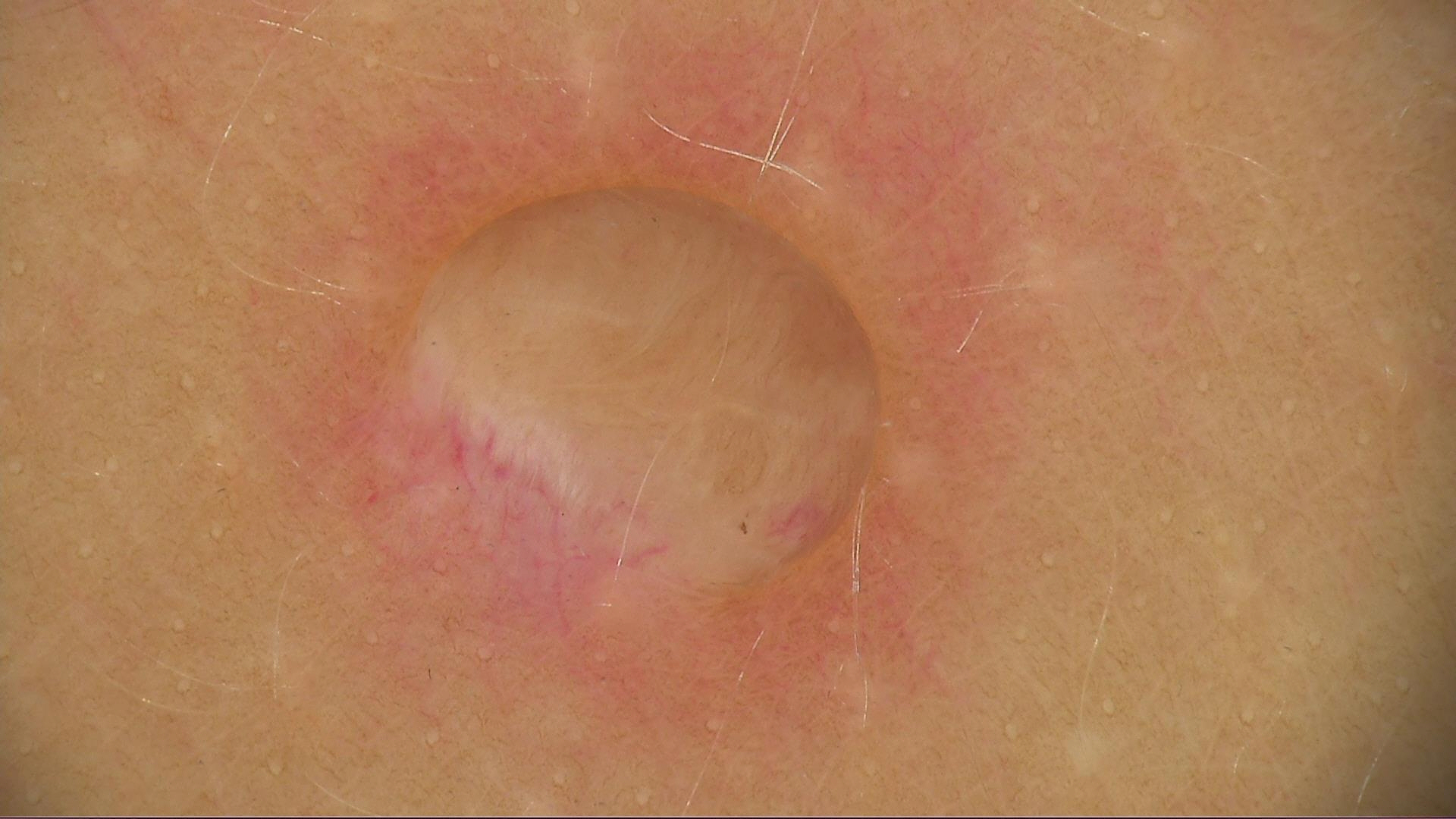Summary:
A dermoscopy image of a single skin lesion.
Impression:
Labeled as a banal lesion — a dermal nevus.